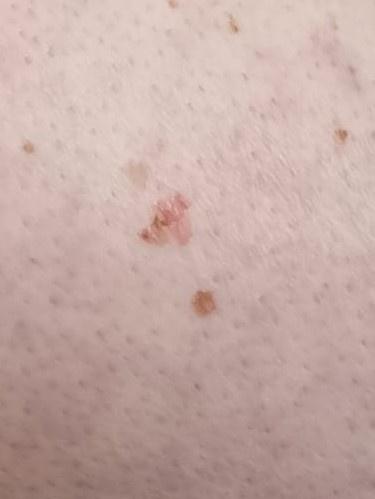Conclusion: Histopathology confirmed a melanoma.